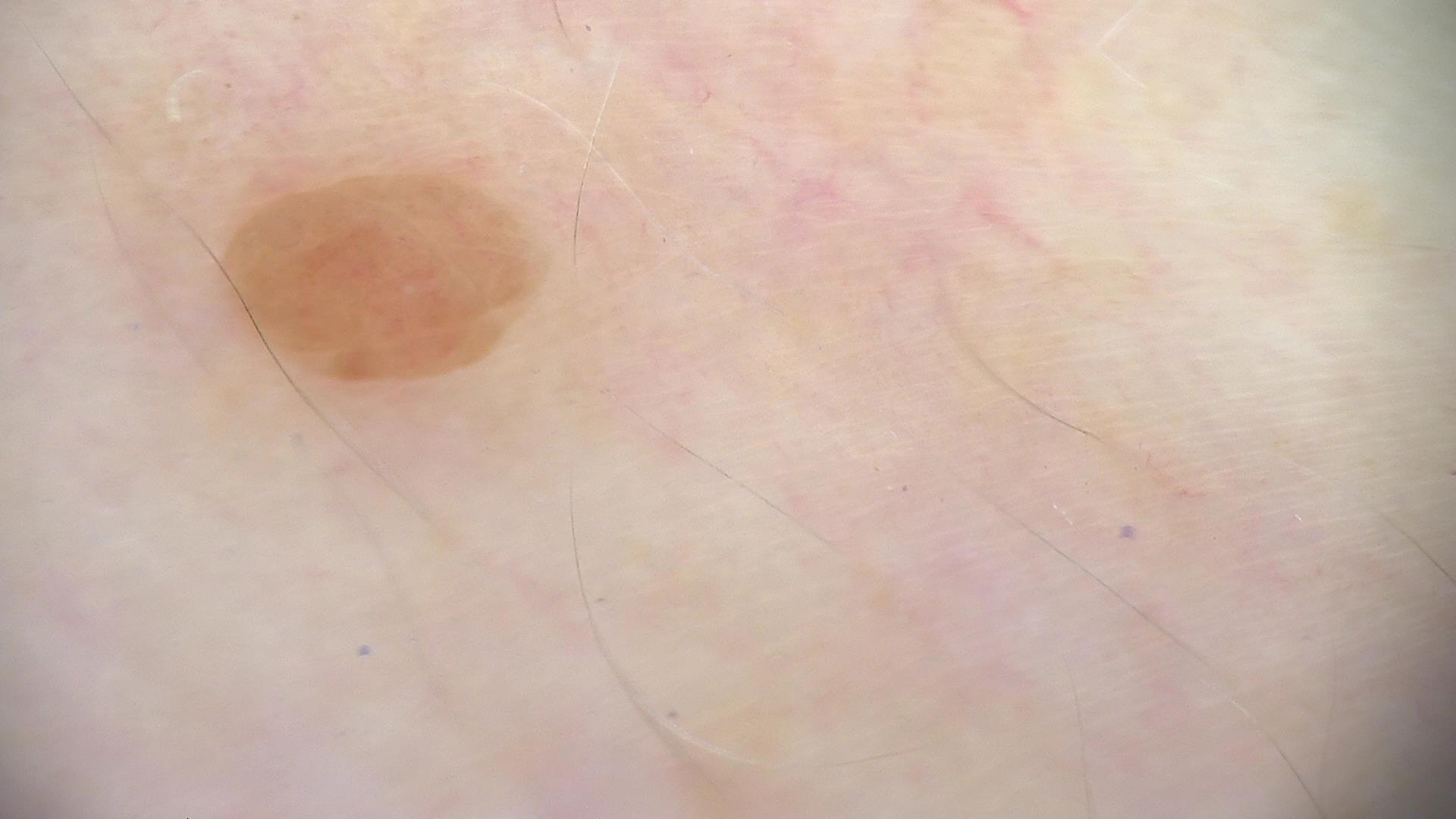class — dermal nevus (expert consensus).